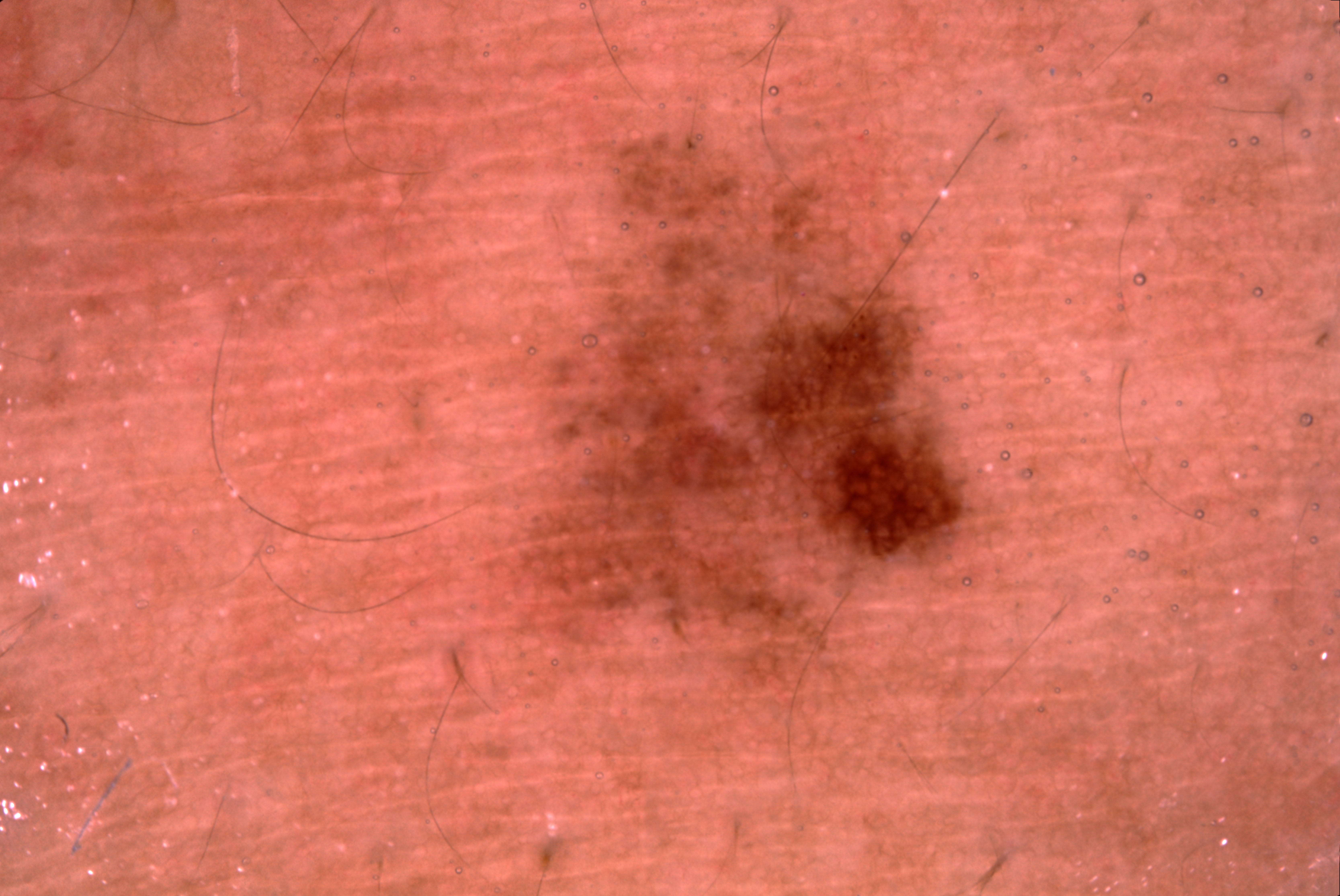A dermatoscopic image of a skin lesion.
A male subject, aged around 40.
As (left, top, right, bottom), the lesion is bounded by <box>506, 135, 983, 694</box>.
Dermoscopically, the lesion shows milia-like cysts and pigment network.
The clinical diagnosis was a melanocytic nevus, a benign skin lesion.